A dermoscopic photograph of a skin lesion:
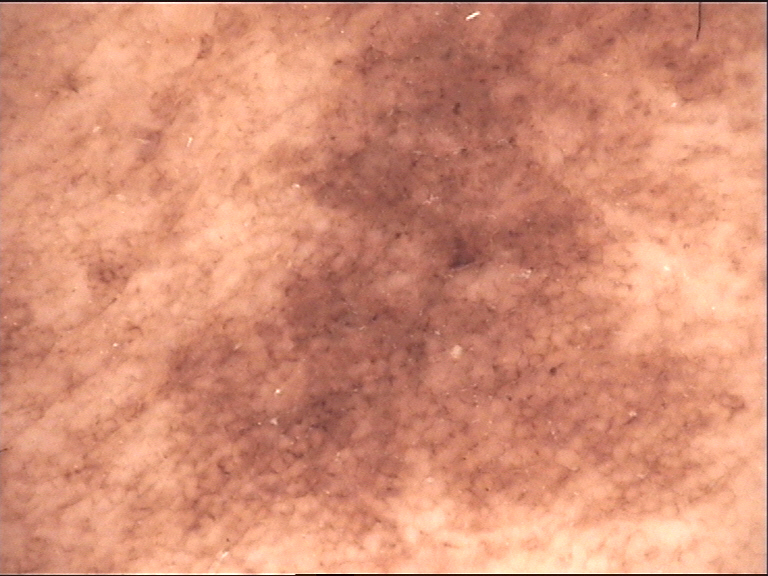subtype = banal
diagnostic label = congenital compound nevus (expert consensus)